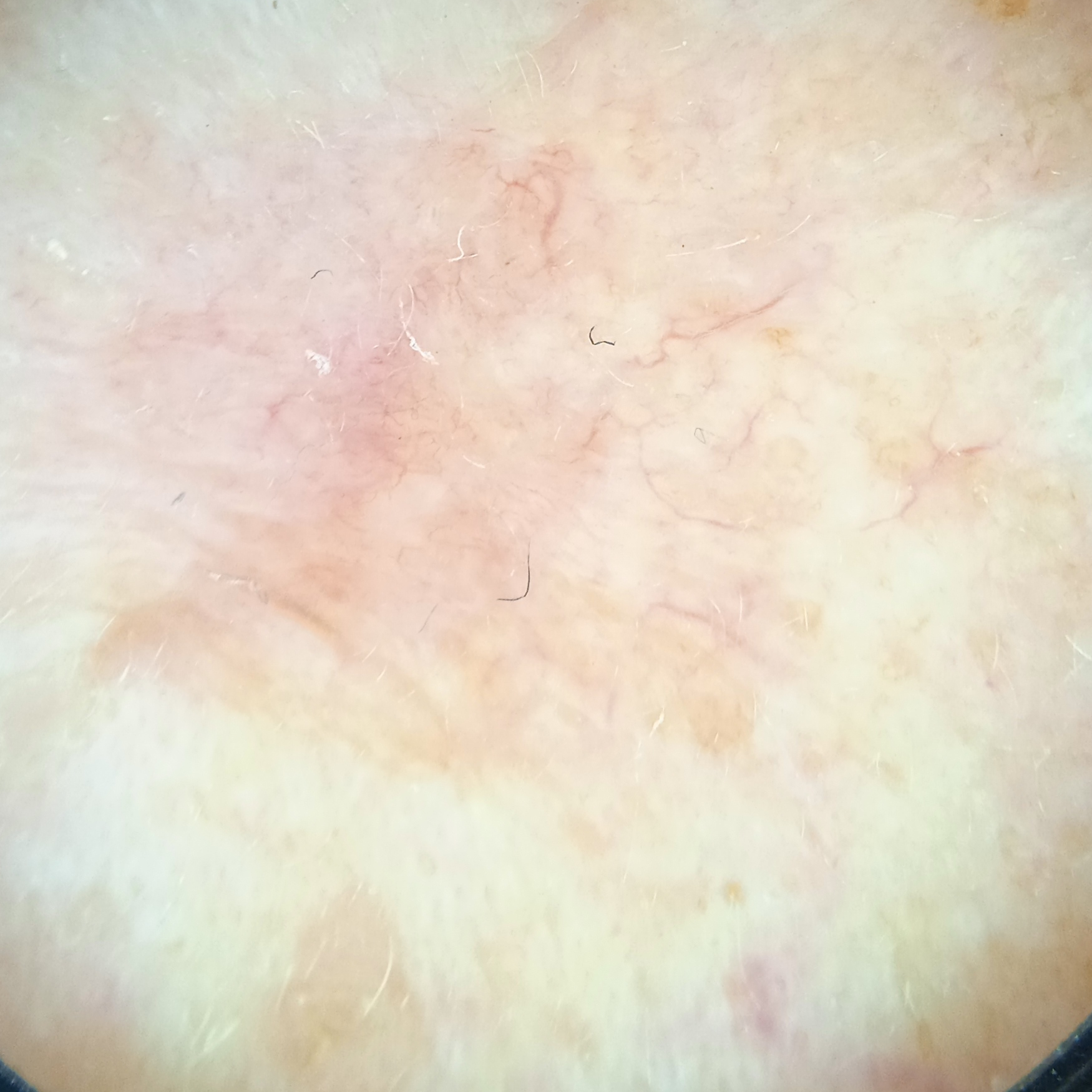The dermatologists' assessment was a basal cell carcinoma.